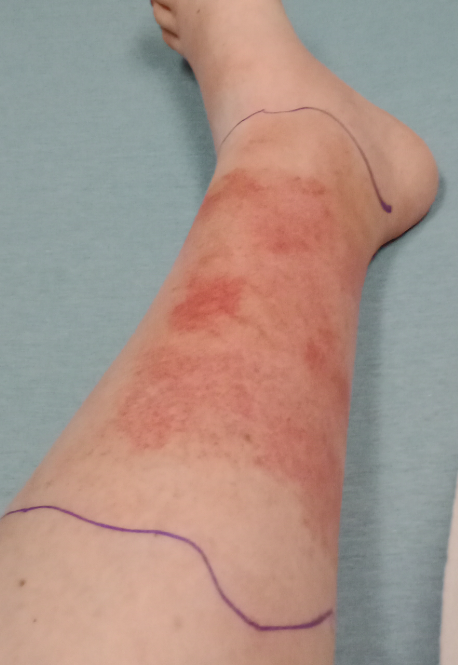The reviewing dermatologists' impression was: the favored diagnosis is Cellulitis; possibly Stasis Dermatitis; also consider Pigmented purpuric eruption.